Close-up view. The patient is 18–29, female. The lesion involves the leg: 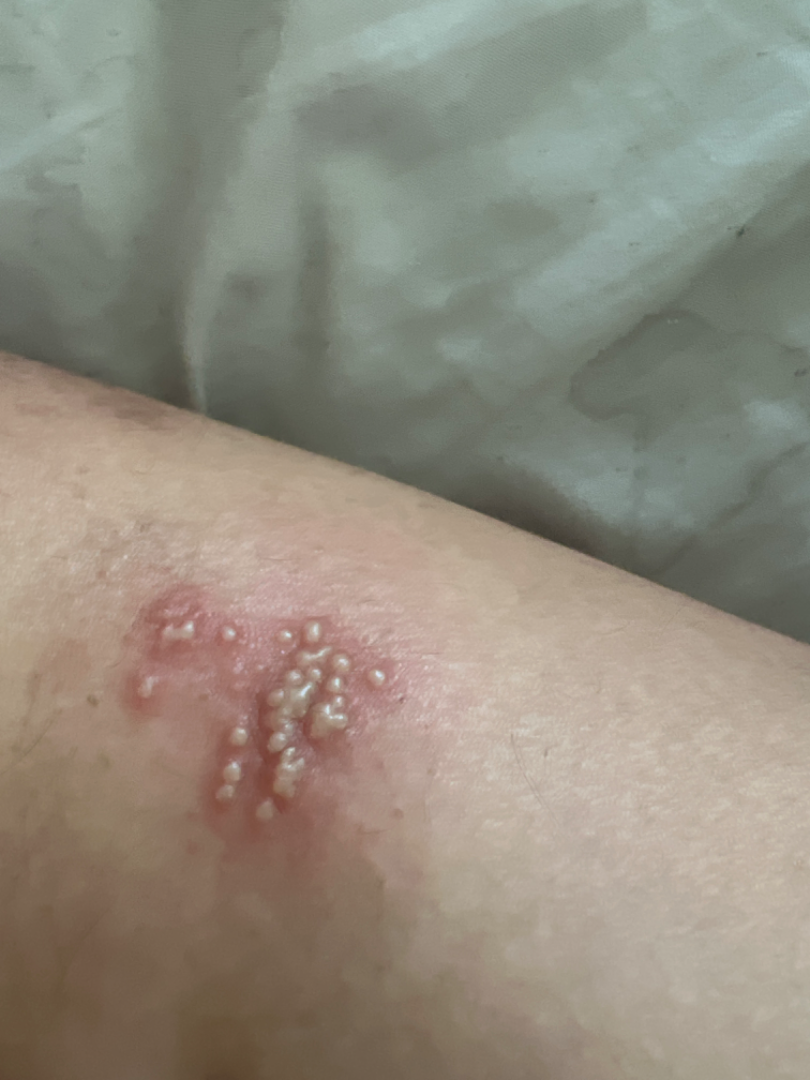Notes:
– dermatologist impression · single-reviewer assessment: most consistent with Herpes Simplex